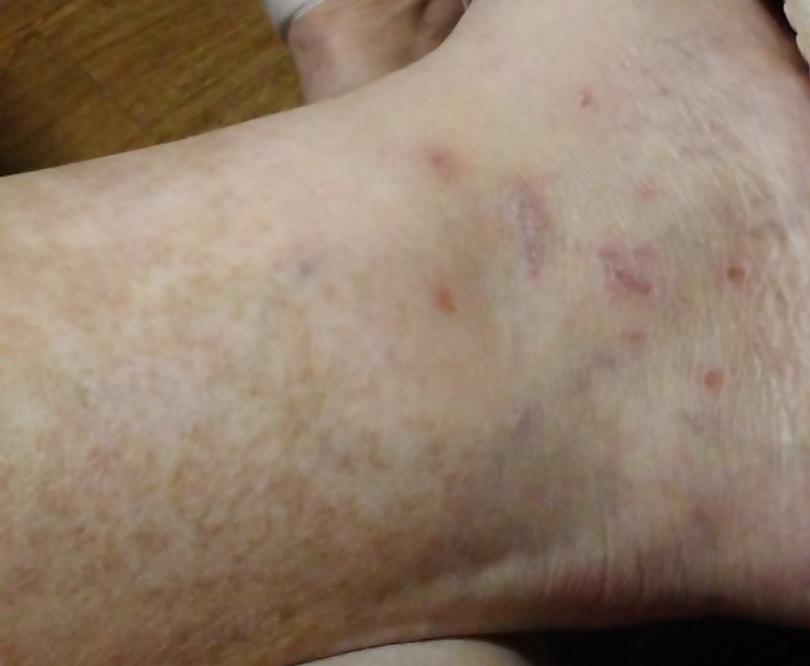assessment: not assessable; patient-reported symptoms: none reported; patient describes the issue as: a rash; symptom duration: more than five years; texture: flat; shot type: close-up; anatomic site: leg; contributor: female, age 40–49.